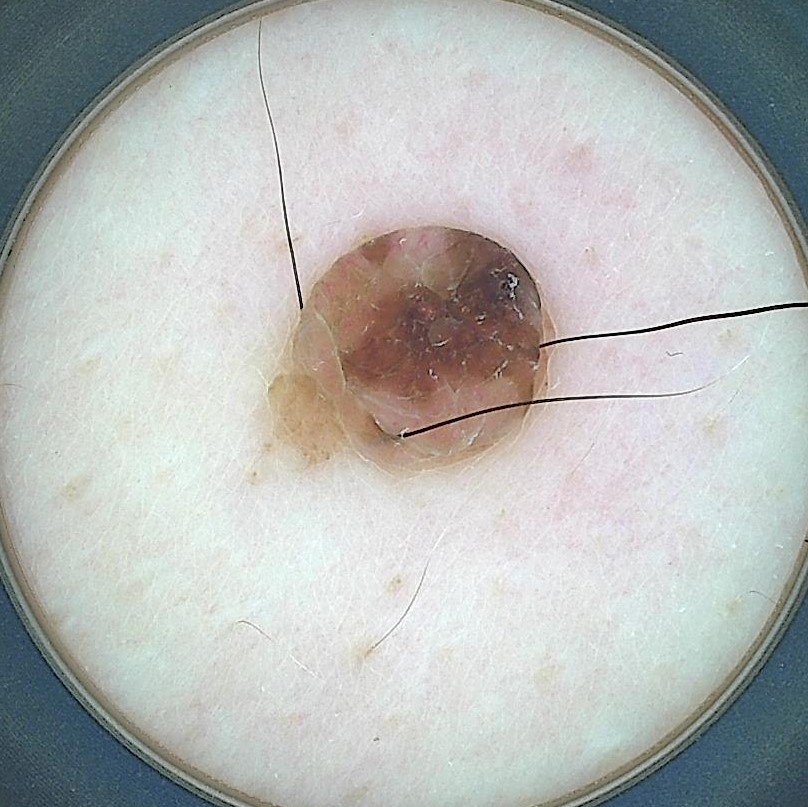A dermoscopic photograph of a skin lesion. The diagnosis was a dermal nevus.